Dermoscopy of a skin lesion.
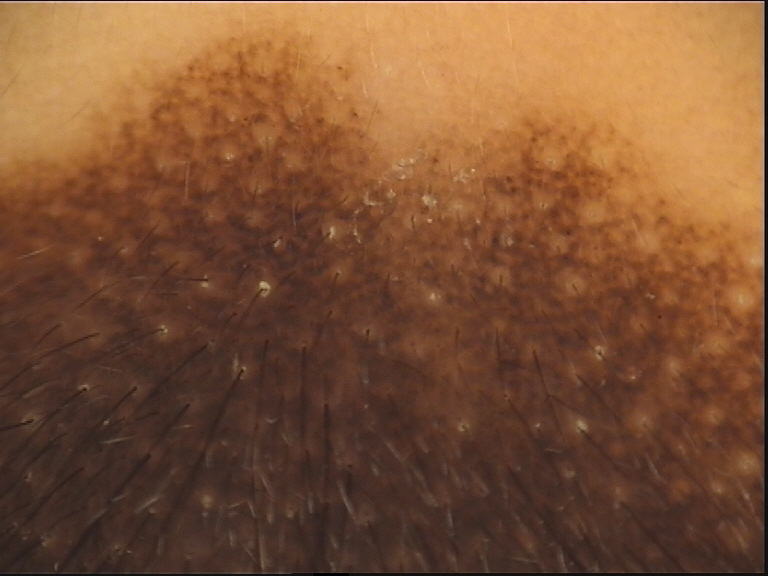diagnosis = congenital compound nevus (expert consensus).